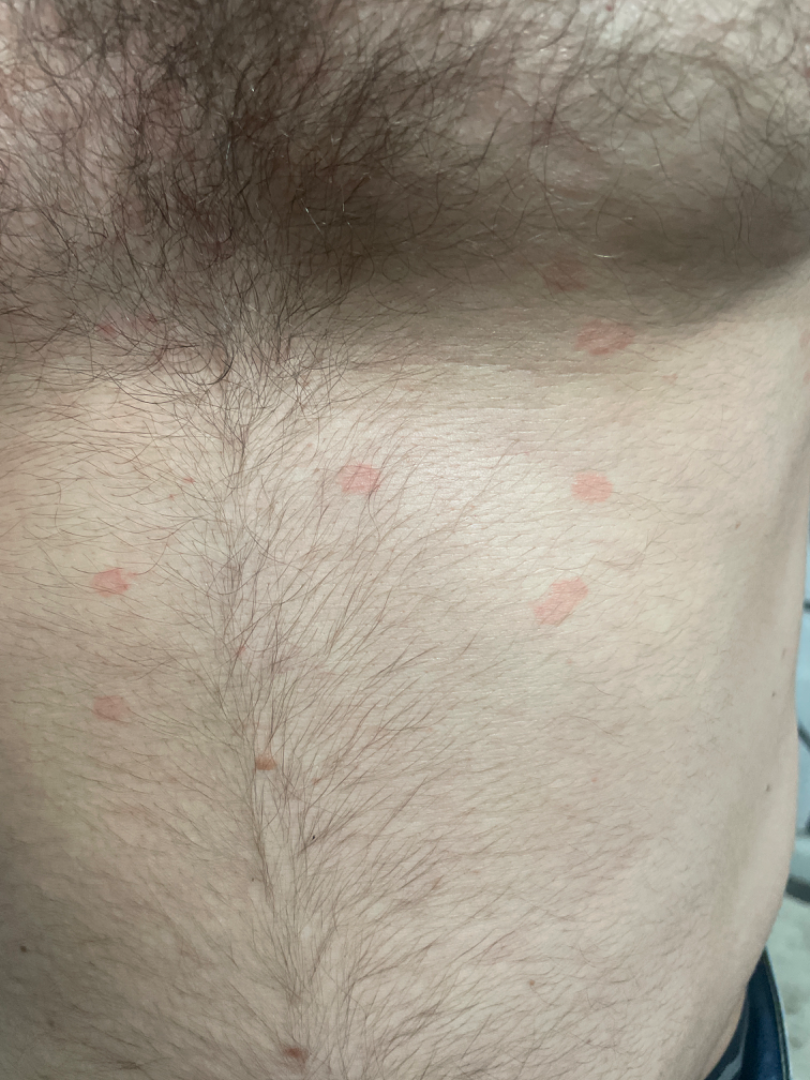<dermatology_case>
<shot_type>at a distance</shot_type>
<differential>
  <leading>Eczema</leading>
  <considered>Pityriasis rosea</considered>
  <unlikely>Psoriasis</unlikely>
</differential>
</dermatology_case>